Female patient, age 50–59 · an image taken at an angle · the lesion involves the leg — 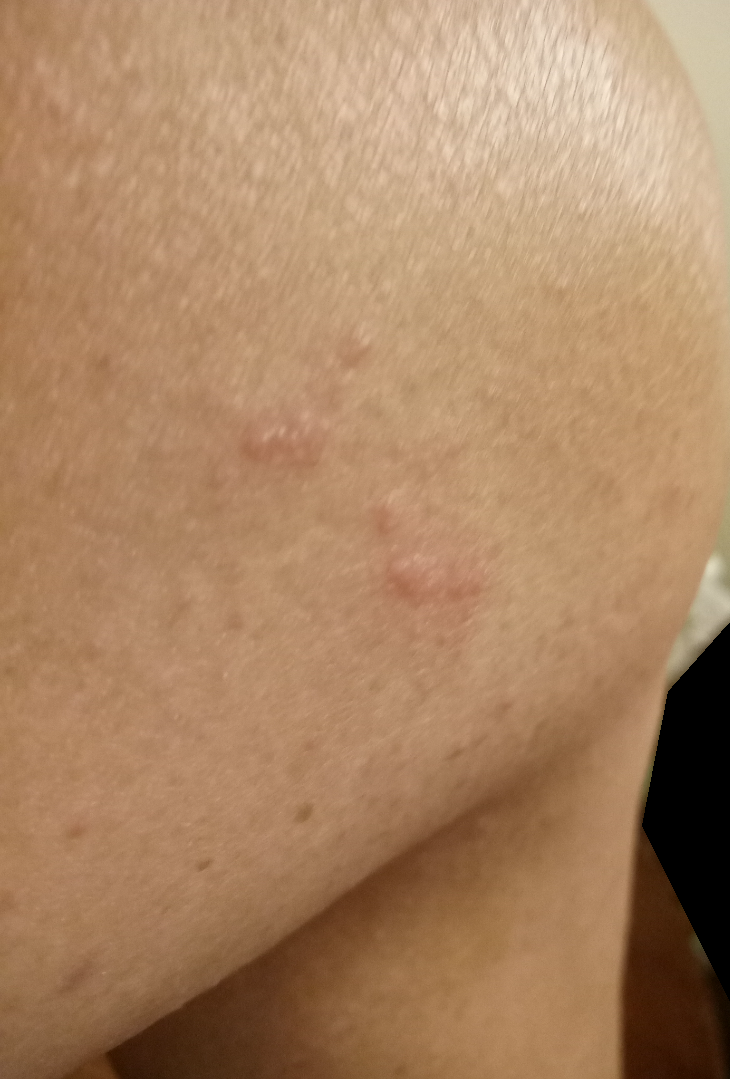Q: Constitutional symptoms?
A: chills
Q: When did this start?
A: about one day
Q: What symptoms does the patient report?
A: enlargement, bothersome appearance and burning
Q: Patient's own categorization?
A: skin that appeared healthy to them
Q: What is the lesion texture?
A: fluid-filled and raised or bumpy
Q: What conditions are considered?
A: Insect Bite (40%); Allergic Contact Dermatitis (40%); Herpes Zoster (20%)